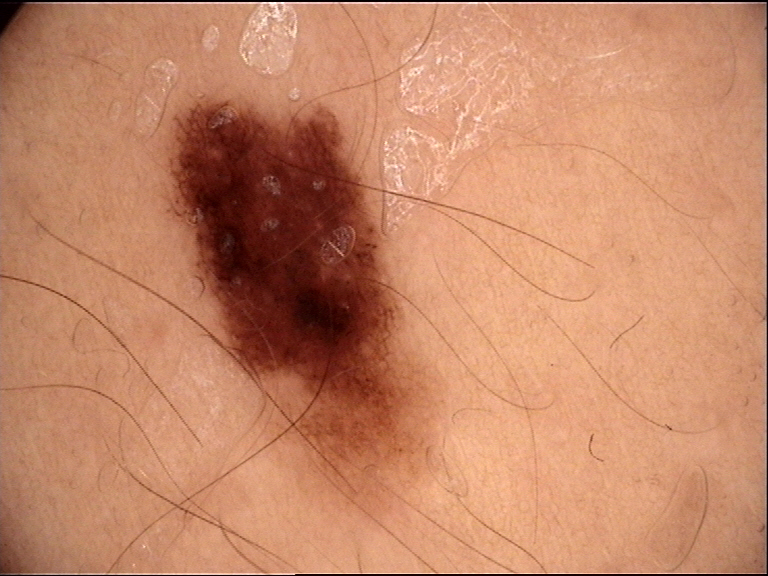Case: A dermoscopic photograph of a skin lesion. Conclusion: The diagnostic label was a dysplastic junctional nevus.